A male subject, roughly 45 years of age. A dermoscopy image of a single skin lesion:
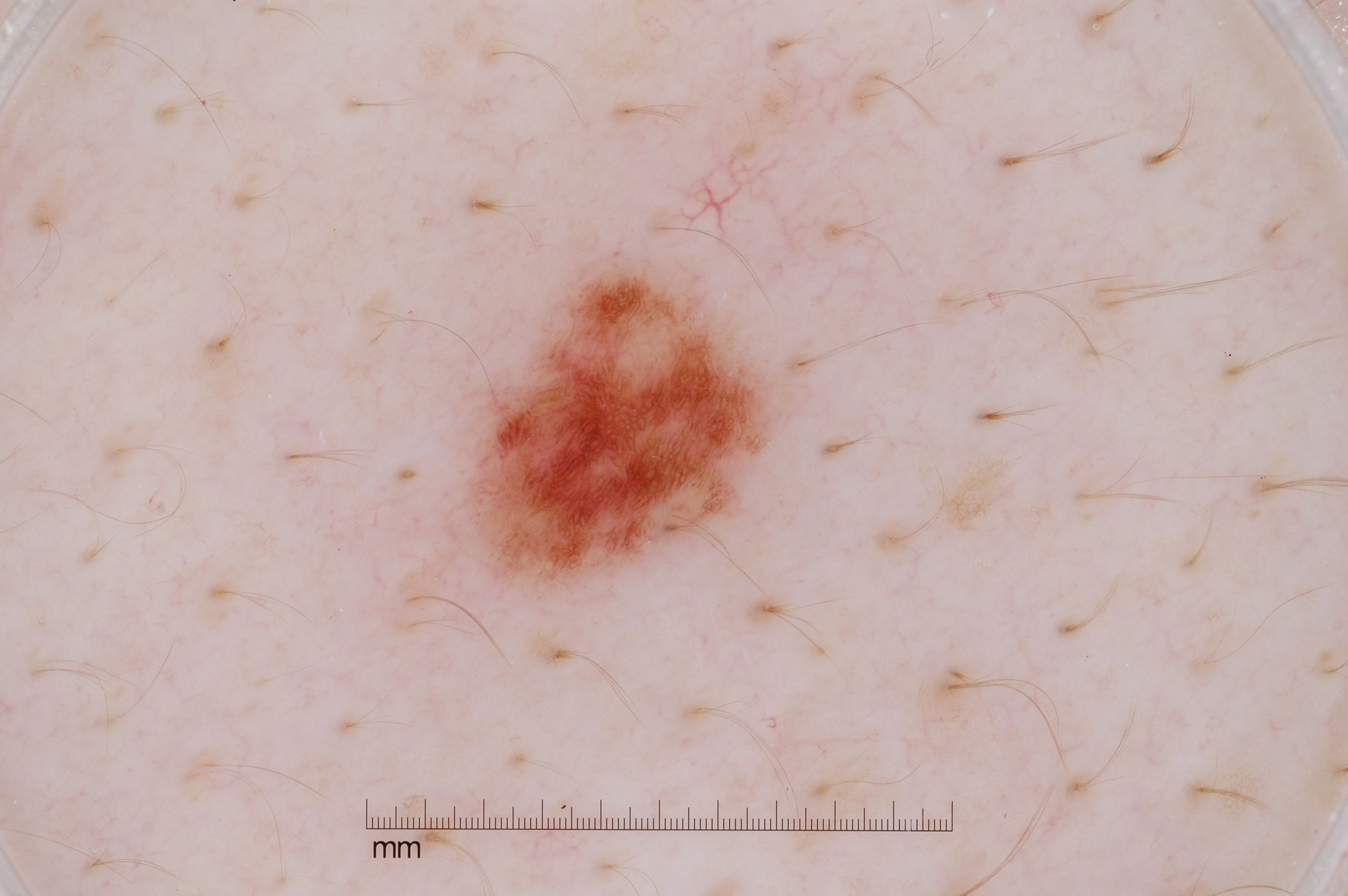lesion bbox = 460/259/788/602 | dermoscopic features = pigment network; absent: milia-like cysts, streaks, and negative network | lesion extent = small | diagnostic label = a melanocytic nevus.